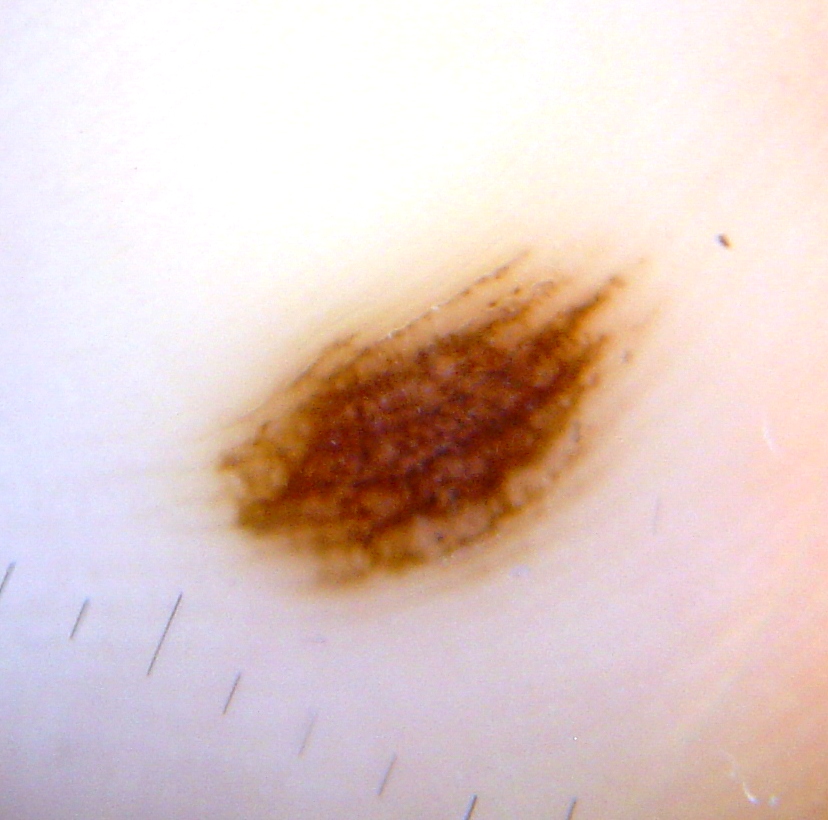Q: What is the diagnosis?
A: acral dysplastic junctional nevus (expert consensus)